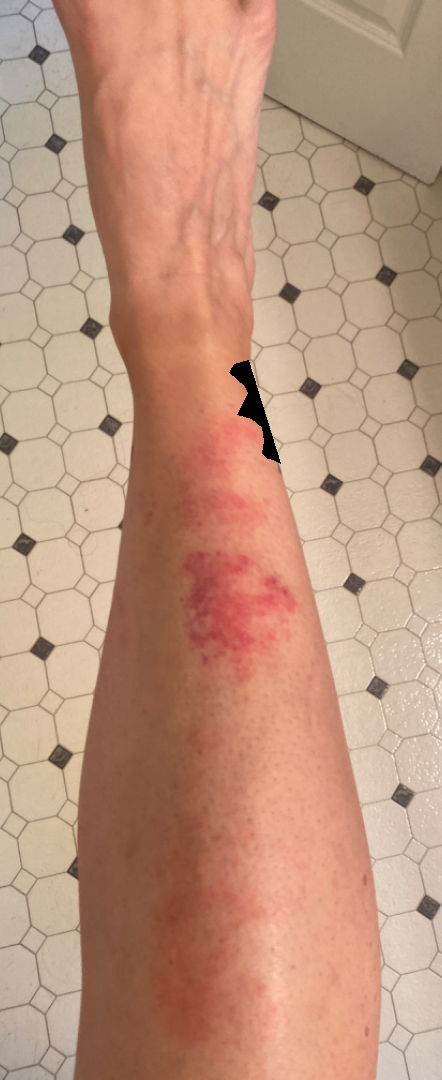differential diagnosis: most consistent with Acute dermatitis, NOS